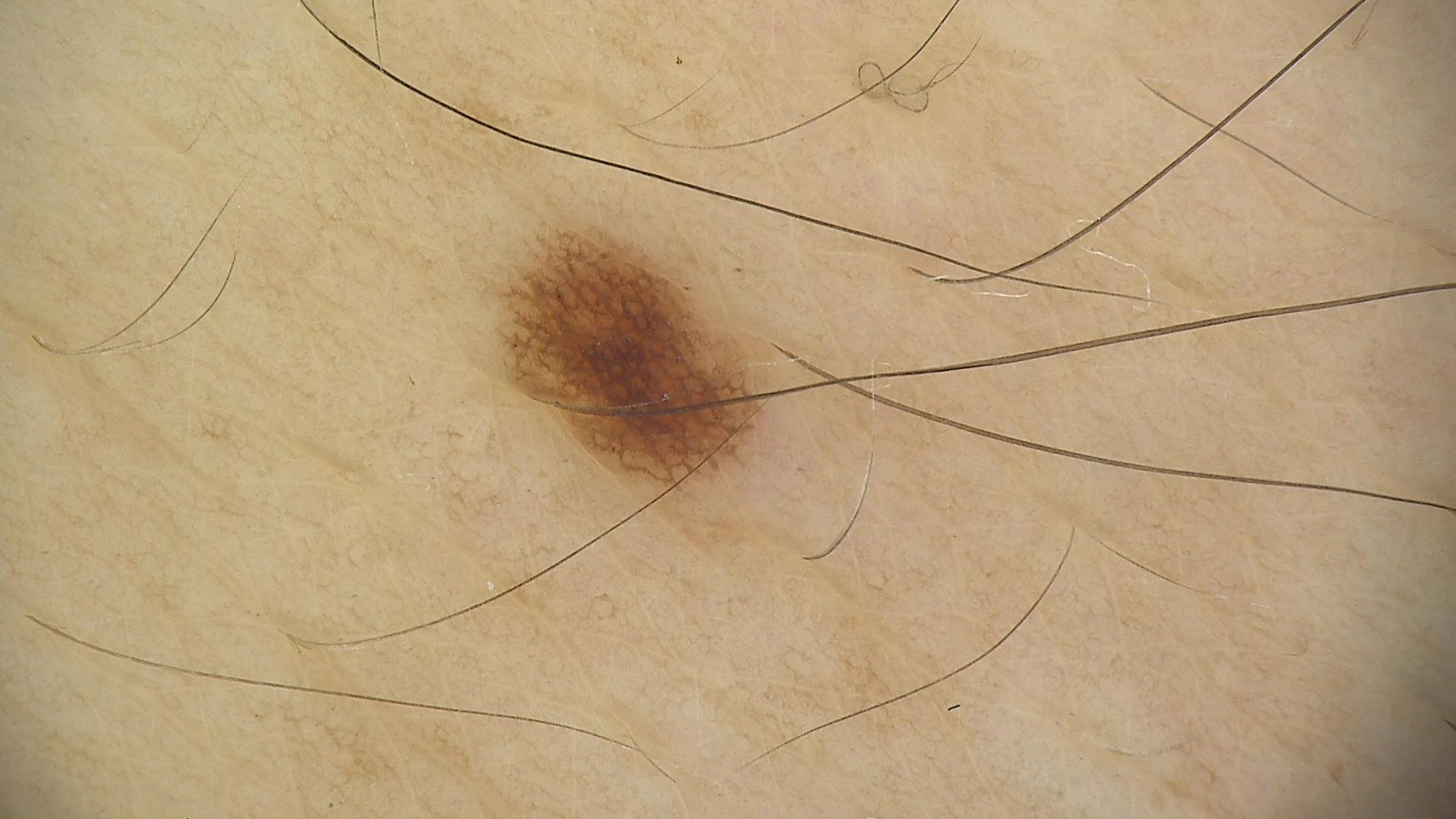Impression: The diagnostic label was a dysplastic junctional nevus.